A dermoscopic photograph of a skin lesion.
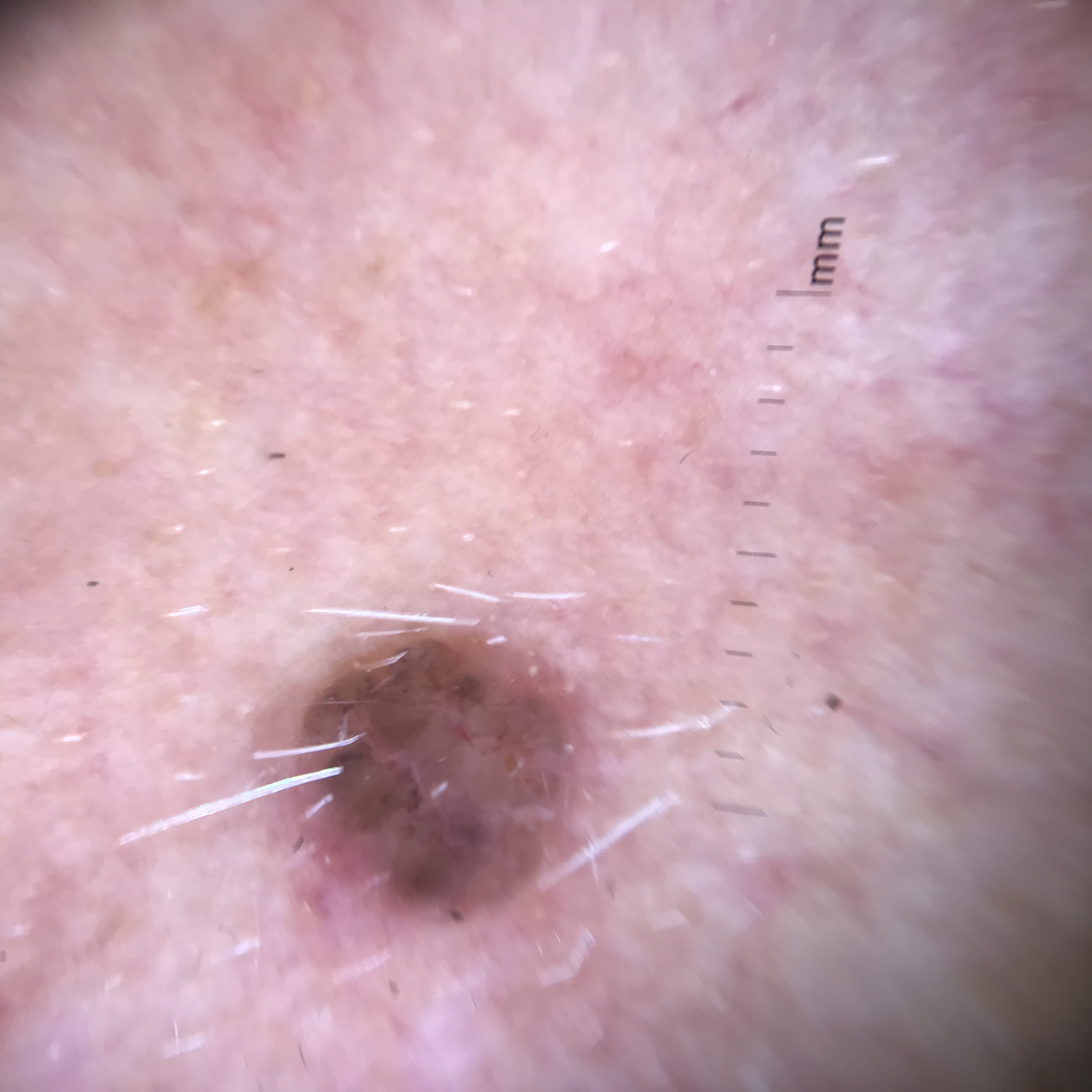Histopathology confirmed a keratinocytic, malignant lesion — a basal cell carcinoma.